A skin lesion imaged with a dermatoscope.
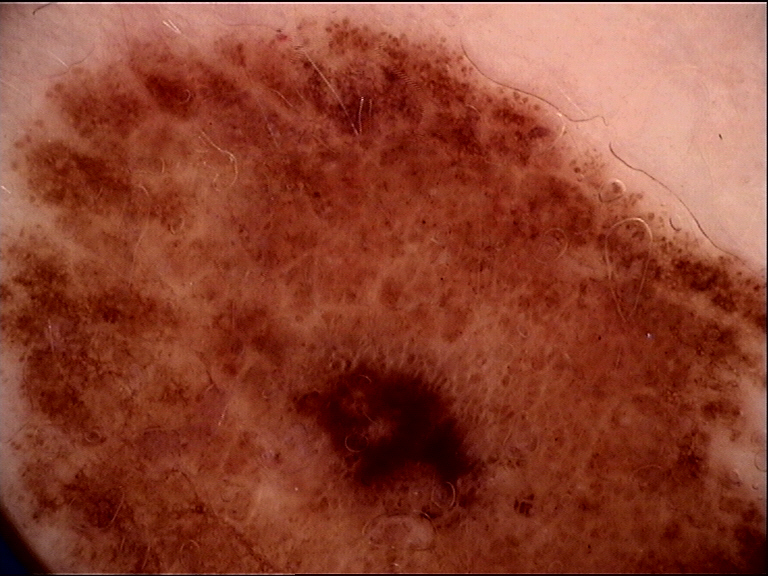Findings:
This is a banal lesion.
Conclusion:
Labeled as a congenital compound nevus.